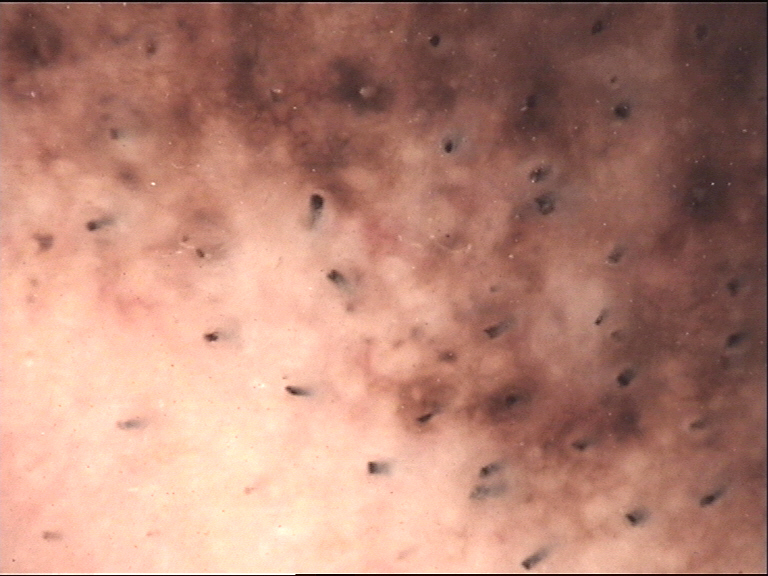<lesion>
  <image>dermoscopy</image>
  <lesion_type>
    <main_class>banal</main_class>
    <pattern>compound</pattern>
  </lesion_type>
  <diagnosis>
    <name>congenital compound nevus</name>
    <code>ccb</code>
    <malignancy>benign</malignancy>
    <super_class>melanocytic</super_class>
    <confirmation>expert consensus</confirmation>
  </diagnosis>
</lesion>